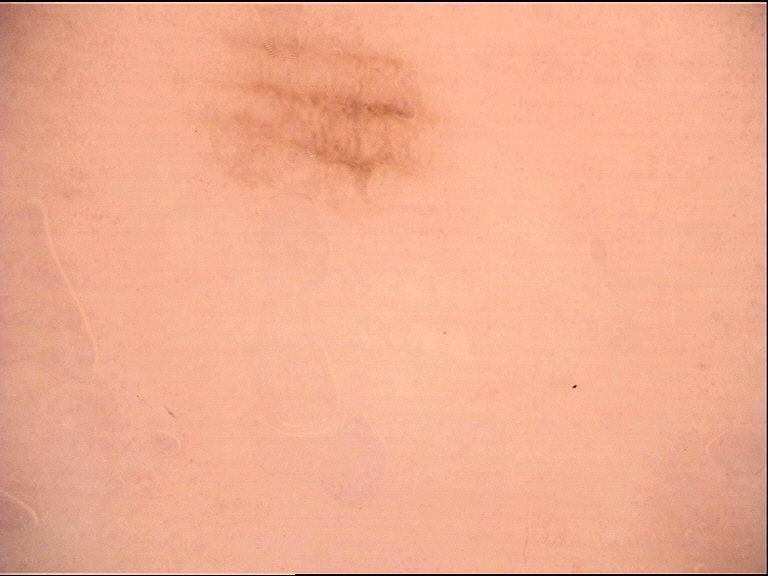Summary: A dermoscopy image of a single skin lesion. Impression: Consistent with a benign lesion — an acral dysplastic junctional nevus.